A skin lesion imaged with a dermatoscope.
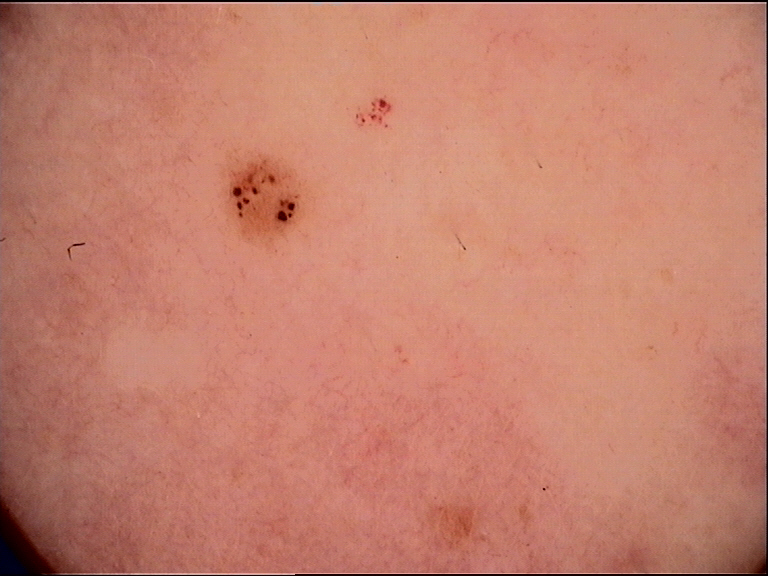label: dysplastic junctional nevus (expert consensus).